Skin tone: FST III; non-clinician graders estimated Monk Skin Tone 4 or 6. Reported lesion symptoms include darkening, bothersome appearance, burning and itching. The photo was captured at an angle. The patient considered this a rash. Reported duration is less than one week. The lesion is described as raised or bumpy and fluid-filled. Located on the arm:
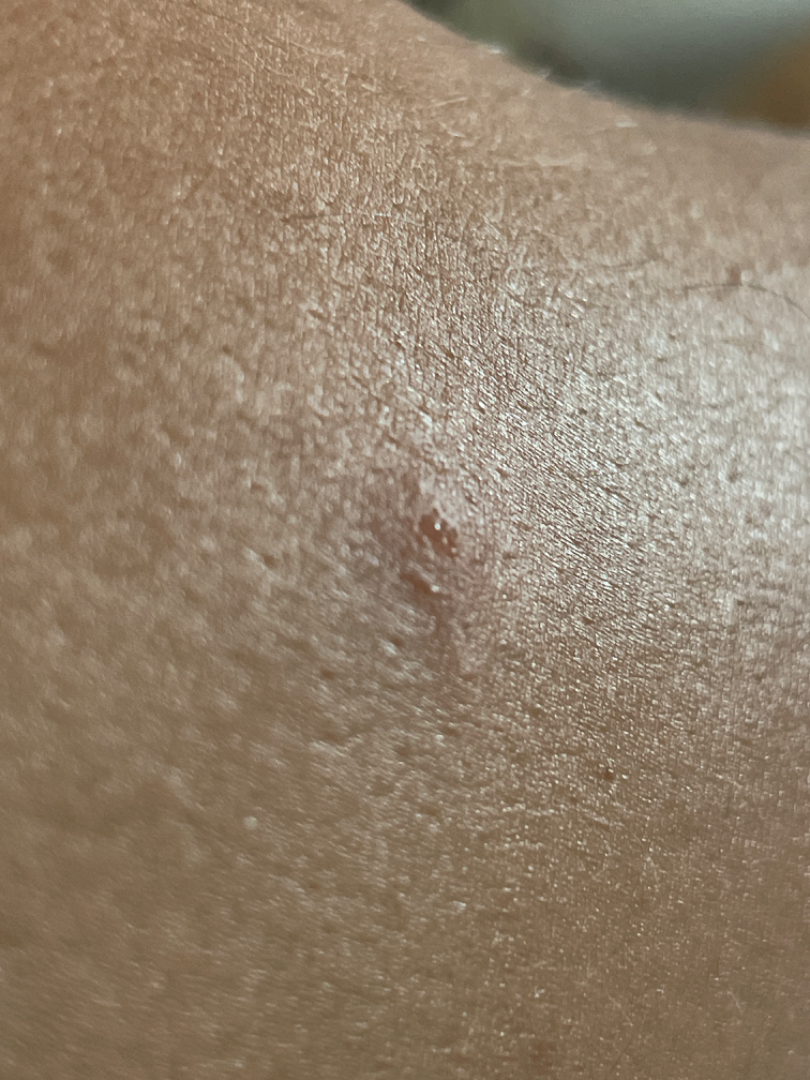  differential:
    tied_lead:
      - Impetigo
      - Insect Bite
      - Allergic Contact Dermatitis